A dermoscopy image of a single skin lesion · a female patient aged around 30 — 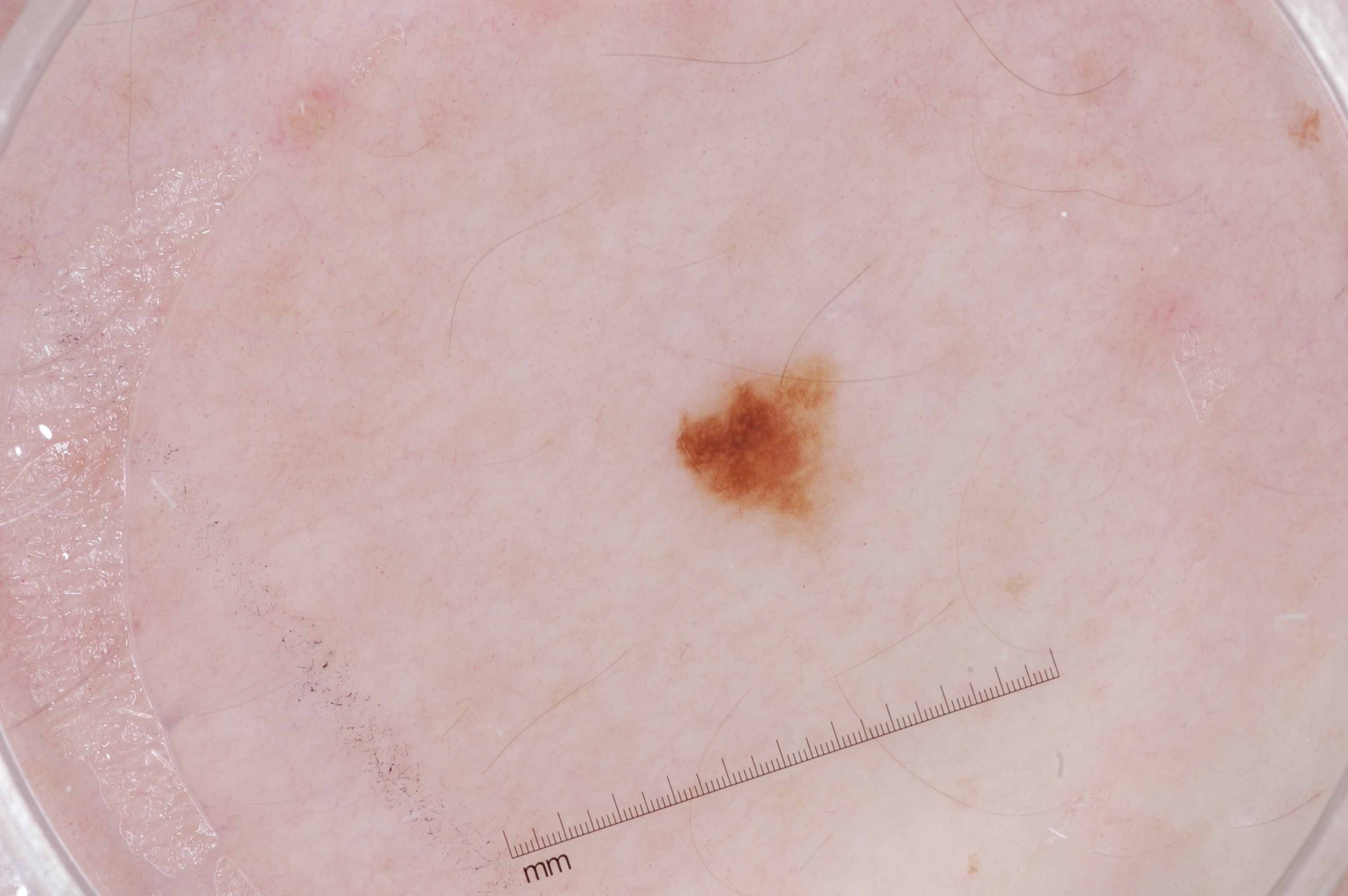lesion location = x1=685, y1=364, x2=842, y2=532 | dermoscopic features not present = negative network, streaks, milia-like cysts, and pigment network | assessment = a melanocytic nevus.